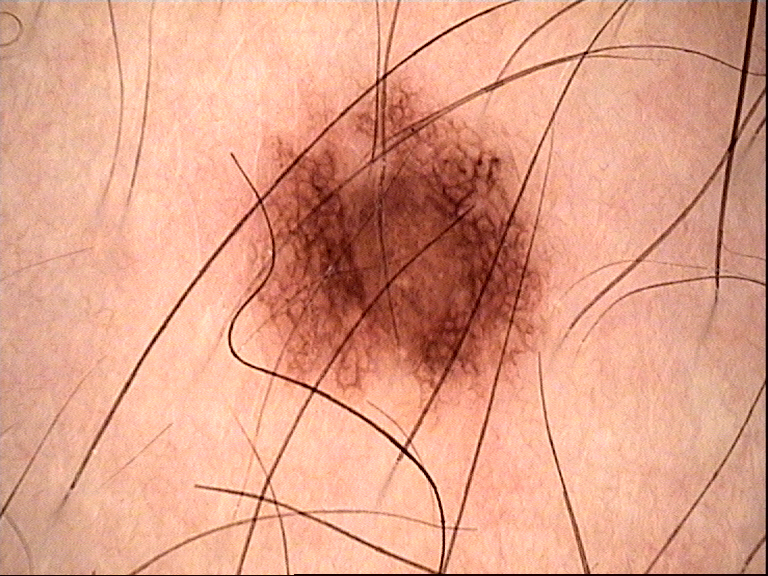Findings: A dermoscopic photograph of a skin lesion. Impression: Classified as a dysplastic junctional nevus.